A close-up photograph · the patient is 30–39, male · the affected area is the arm and leg · the patient described the issue as a rash · the contributor reports the lesion is raised or bumpy · present for less than one week · symptoms reported: itching · skin tone: Fitzpatrick skin type V; non-clinician graders estimated Monk Skin Tone 4–5: 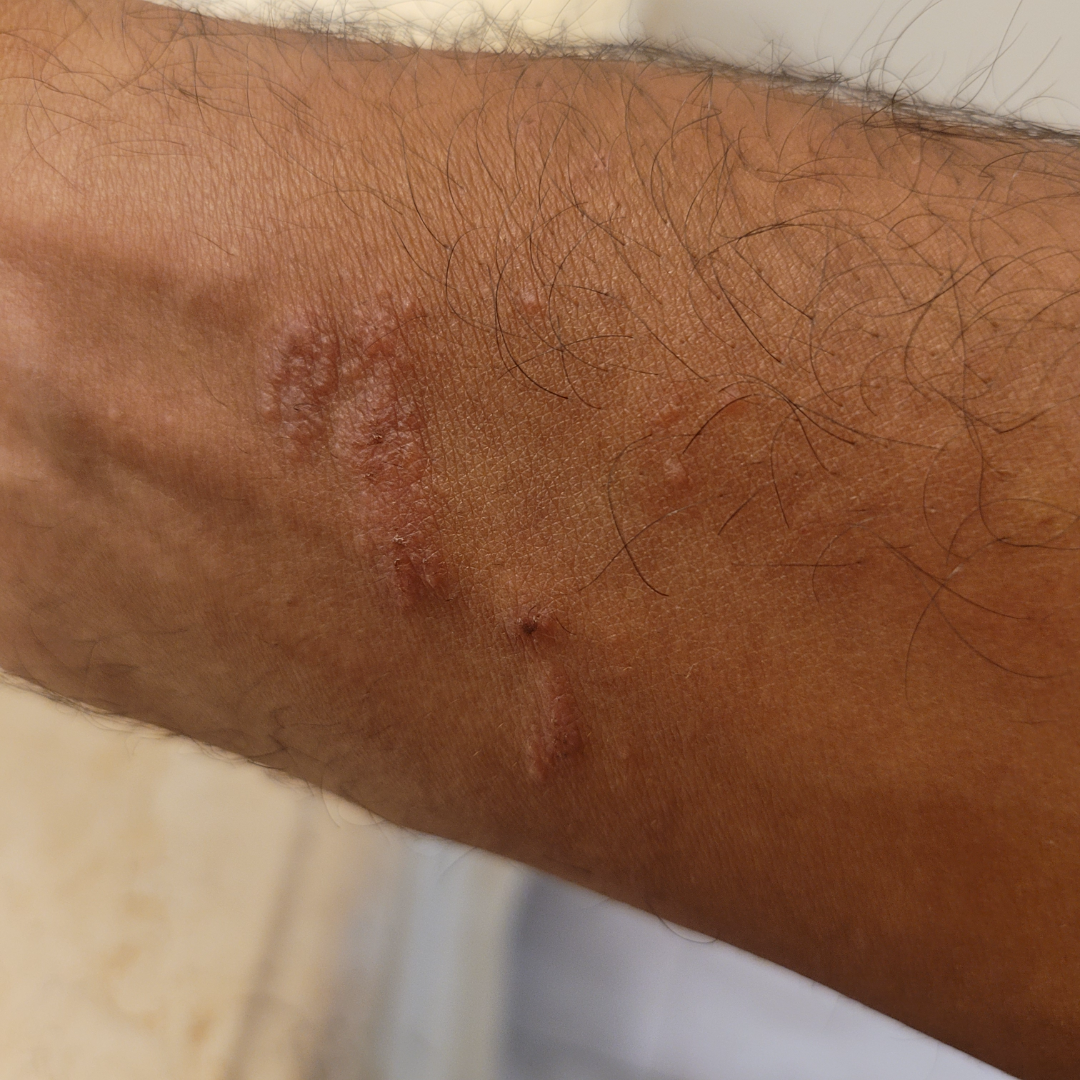assessment — ungradable on photographic review.